The photo was captured at an angle.
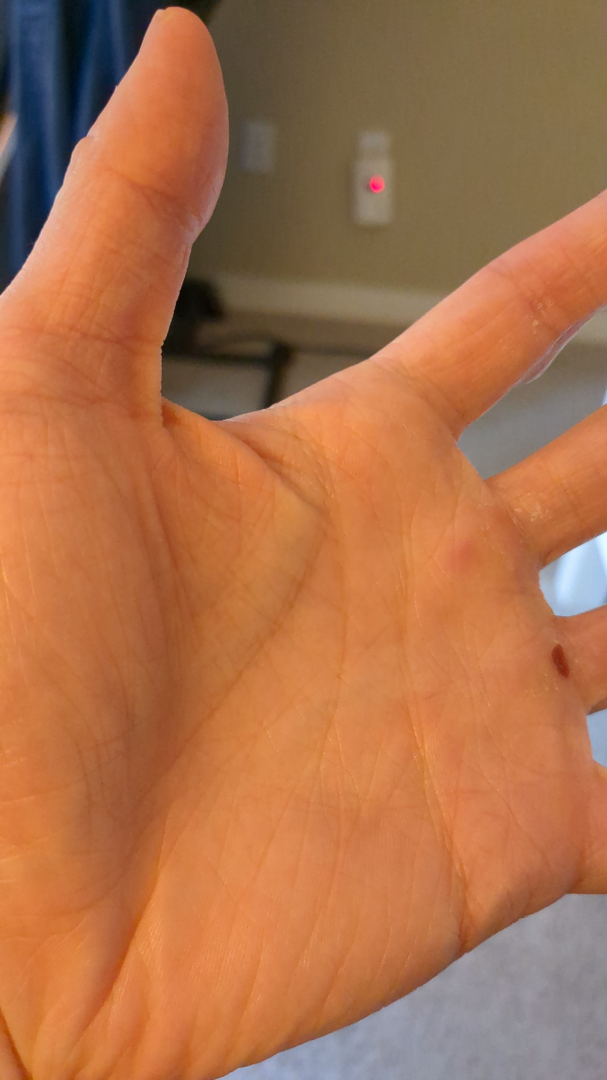Diagnostic features were not clearly distinguishable in this photograph.